A dermatoscopic image of a skin lesion.
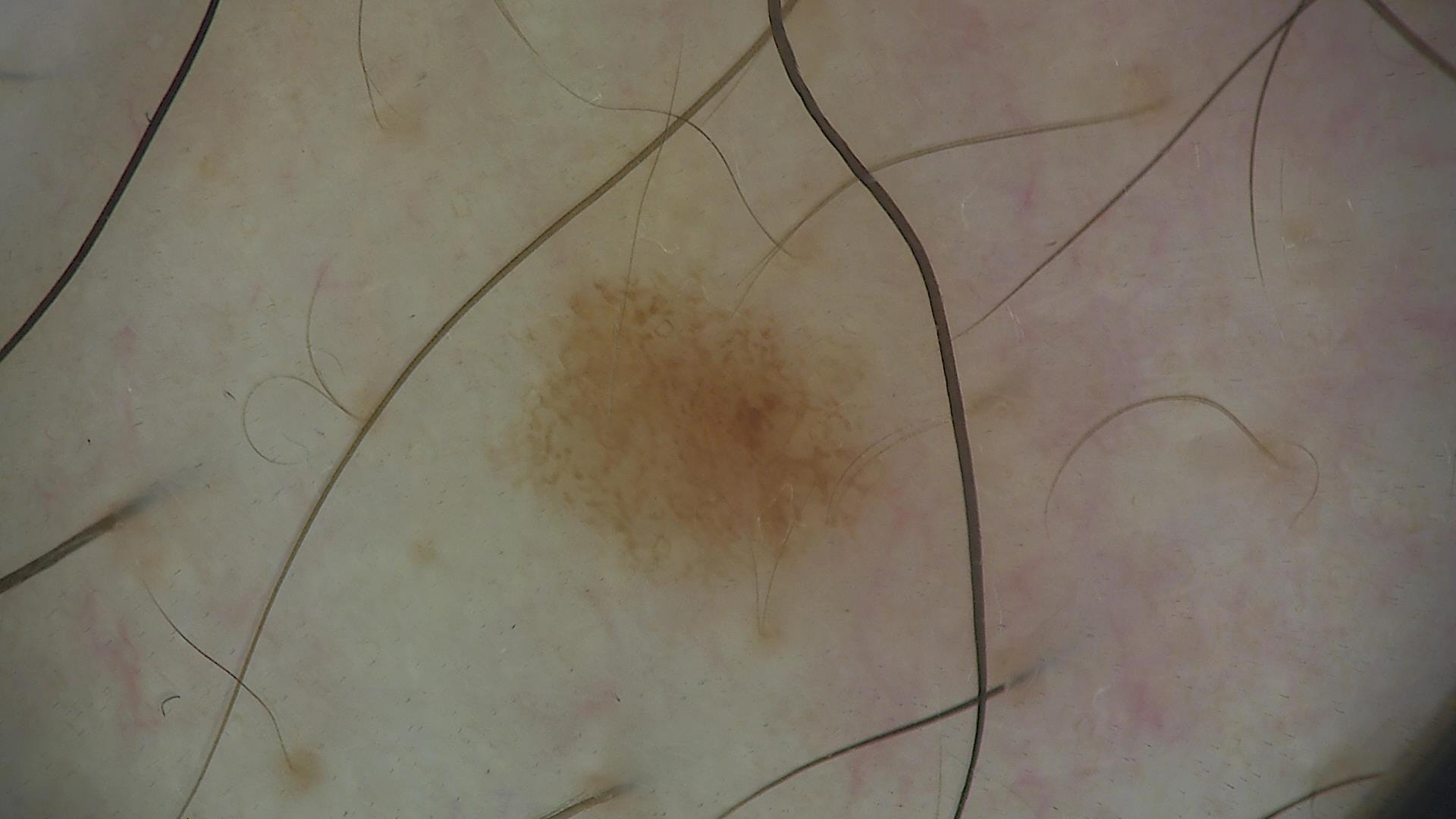Impression:
Classified as a dysplastic junctional nevus.